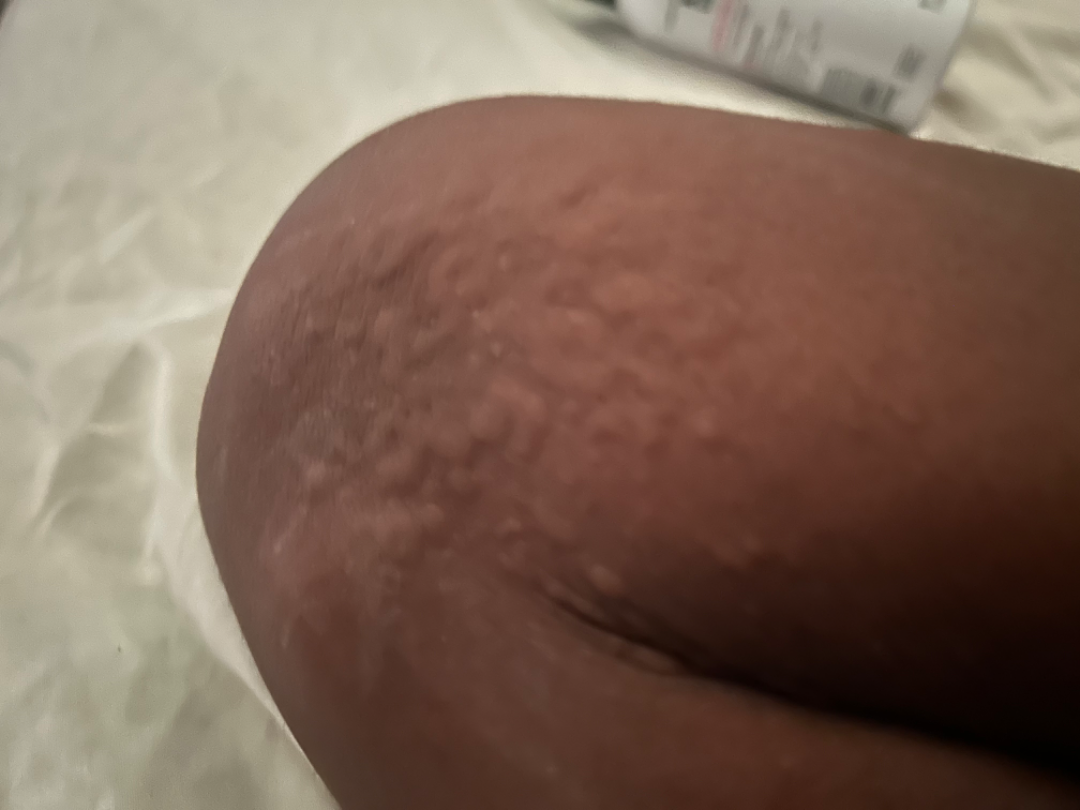Impression:
The primary impression is Urticaria; the differential also includes Allergic Contact Dermatitis.